A dermoscopic image of a skin lesion.
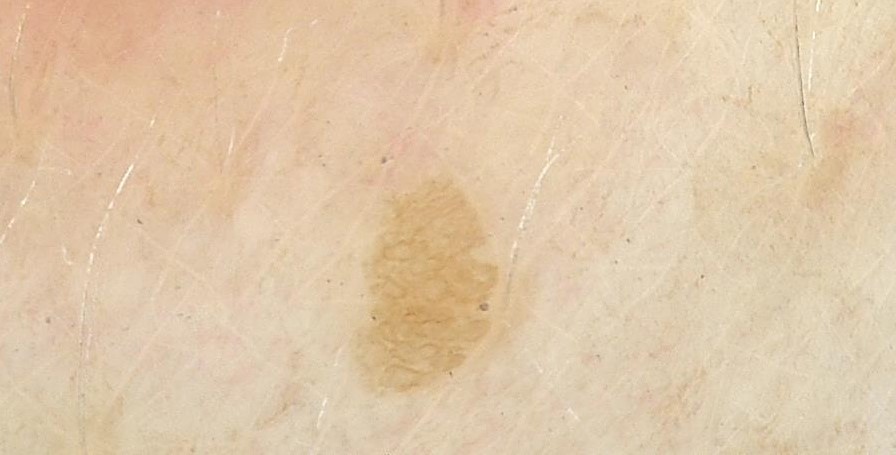Labeled as a keratinocytic lesion — a seborrheic keratosis.